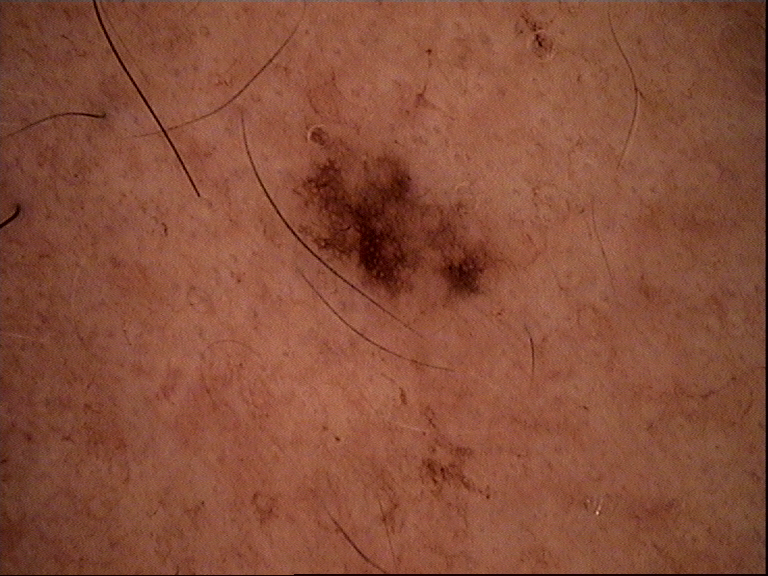<lesion>
  <image>dermoscopy</image>
  <diagnosis>
    <name>dysplastic junctional nevus</name>
    <code>jd</code>
    <malignancy>benign</malignancy>
    <super_class>melanocytic</super_class>
    <confirmation>expert consensus</confirmation>
  </diagnosis>
</lesion>